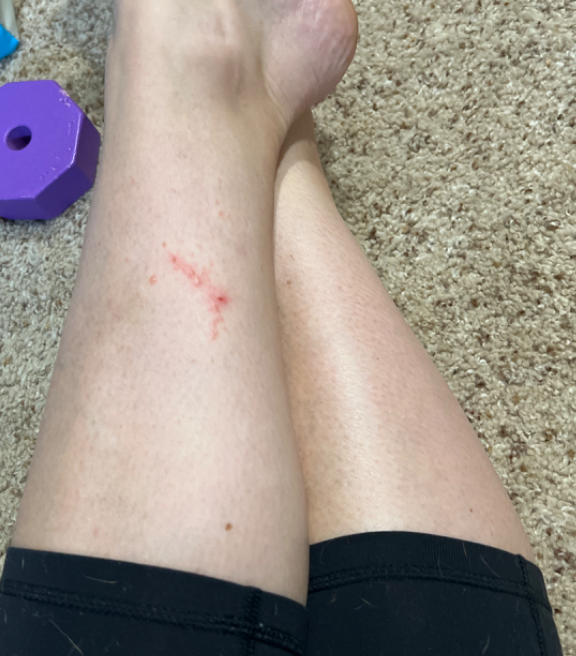texture = fluid-filled and raised or bumpy
anatomic site = leg
shot type = at a distance
patient-reported symptoms = bothersome appearance, pain and itching
patient describes the issue as = a rash
assessment = Cutaneous larva migrans (considered); Allergic Contact Dermatitis (considered); Localized skin infection (lower probability)